A dermoscopic image of a skin lesion: 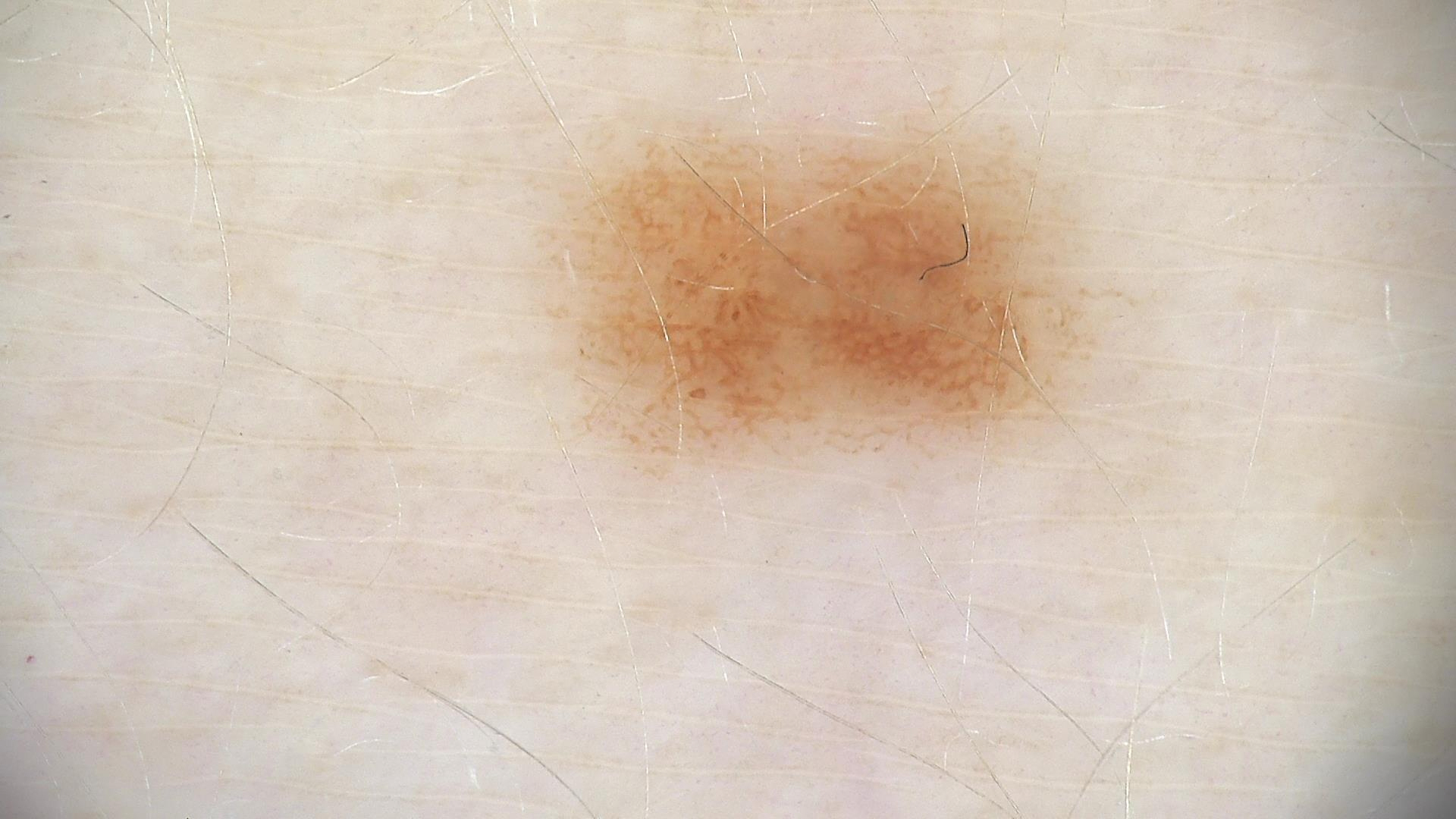Labeled as a dysplastic junctional nevus.